A dermoscopic image of a skin lesion:
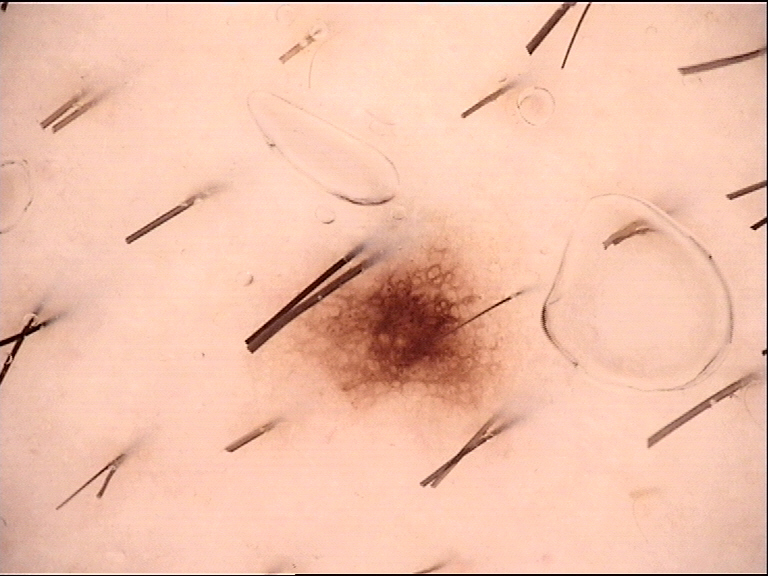{"diagnosis": {"name": "dysplastic junctional nevus", "code": "jd", "malignancy": "benign", "super_class": "melanocytic", "confirmation": "expert consensus"}}